Dermoscopy of a skin lesion.
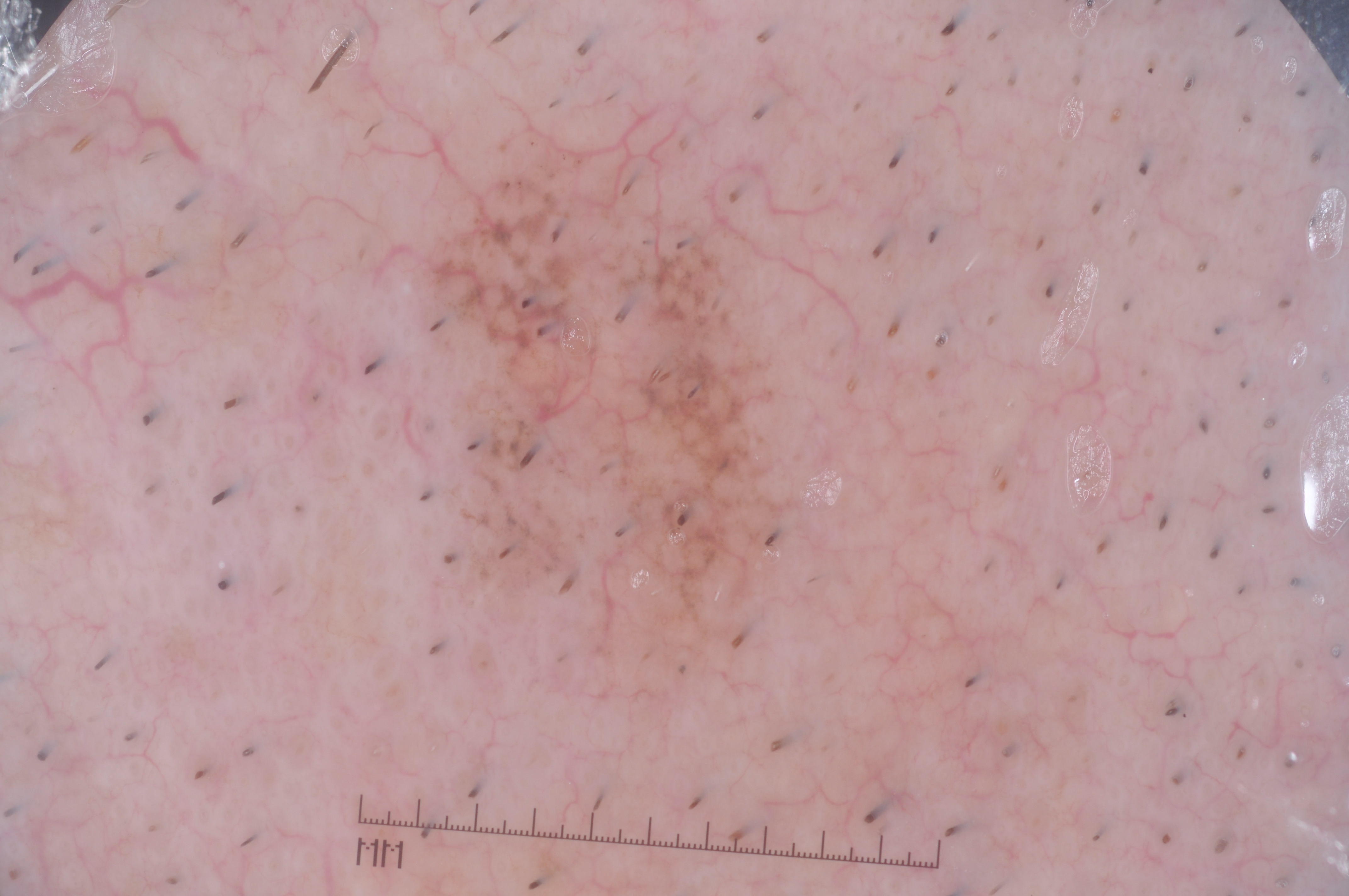Findings:
• dermoscopic findings — milia-like cysts; absent: negative network, pigment network, and streaks
• lesion location — box(422, 119, 801, 672)
• assessment — a melanoma